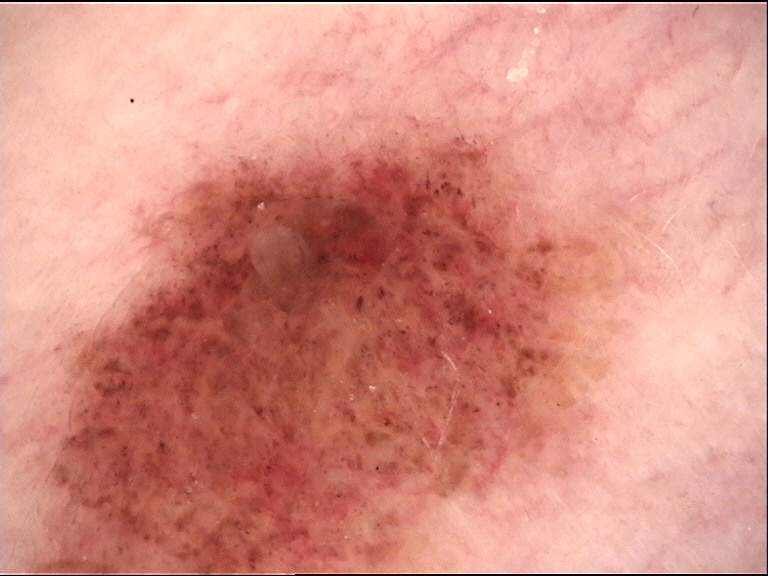Consistent with a dysplastic compound nevus.